An image taken at a distance; female patient, age 30–39; the condition has been present for one to three months; associated systemic symptoms include fatigue and joint pain; the patient described the issue as a rash; the affected area is the arm; symptoms reported: itching:
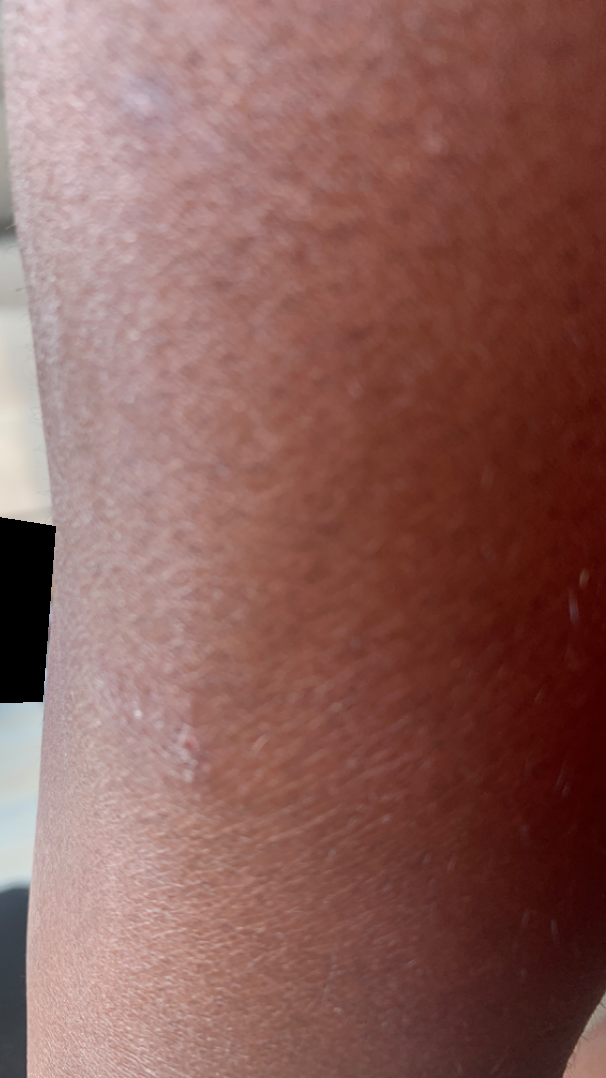differential diagnosis: Psoriasis and Eczema were considered with similar weight.